The patient described the issue as skin that appeared healthy to them; no constitutional symptoms were reported; a close-up photograph; the lesion is described as raised or bumpy; the lesion is associated with enlargement, itching and burning; the arm is involved.
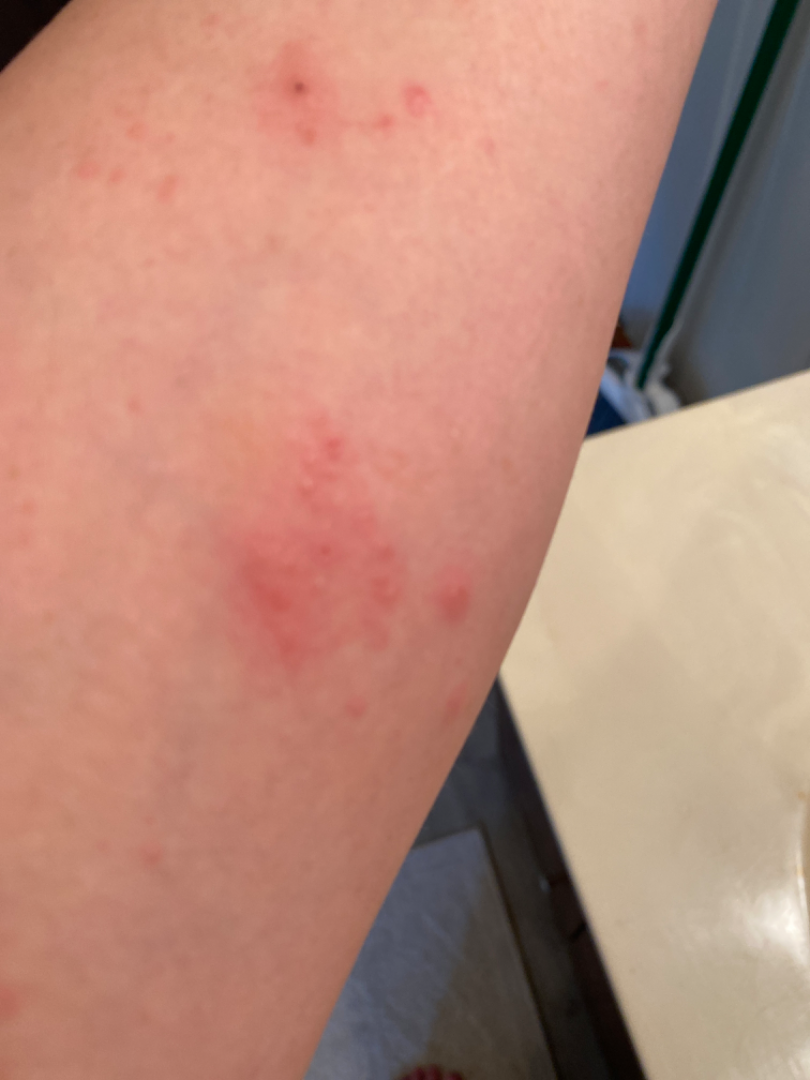On photographic review, the primary impression is Allergic Contact Dermatitis; an alternative is Herpes Zoster; the differential also includes Eczema.